A skin lesion imaged with a dermatoscope.
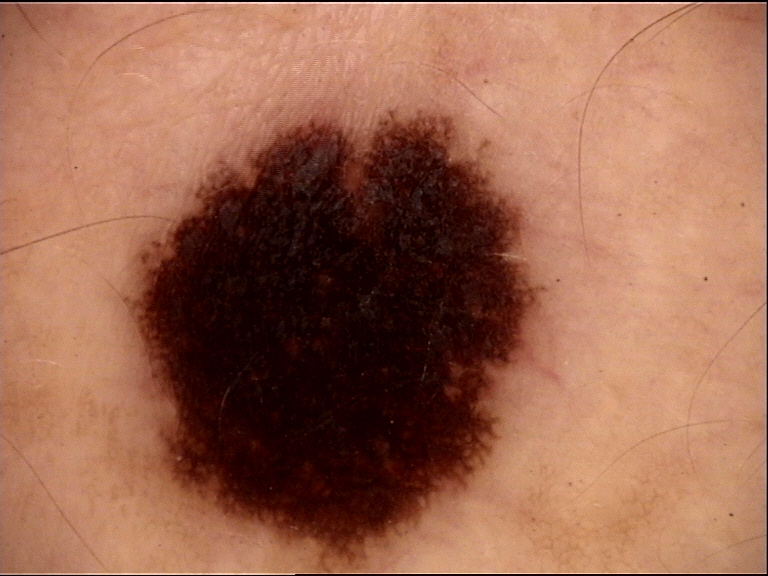assessment — dysplastic junctional nevus (expert consensus).